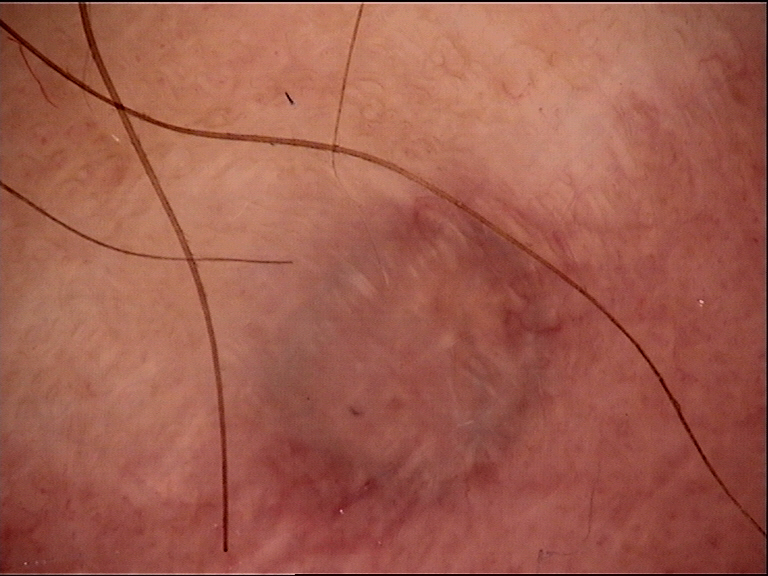image type — dermoscopy | category — banal, dermal | assessment — blue nevus (expert consensus).